A dermoscopic close-up of a skin lesion.
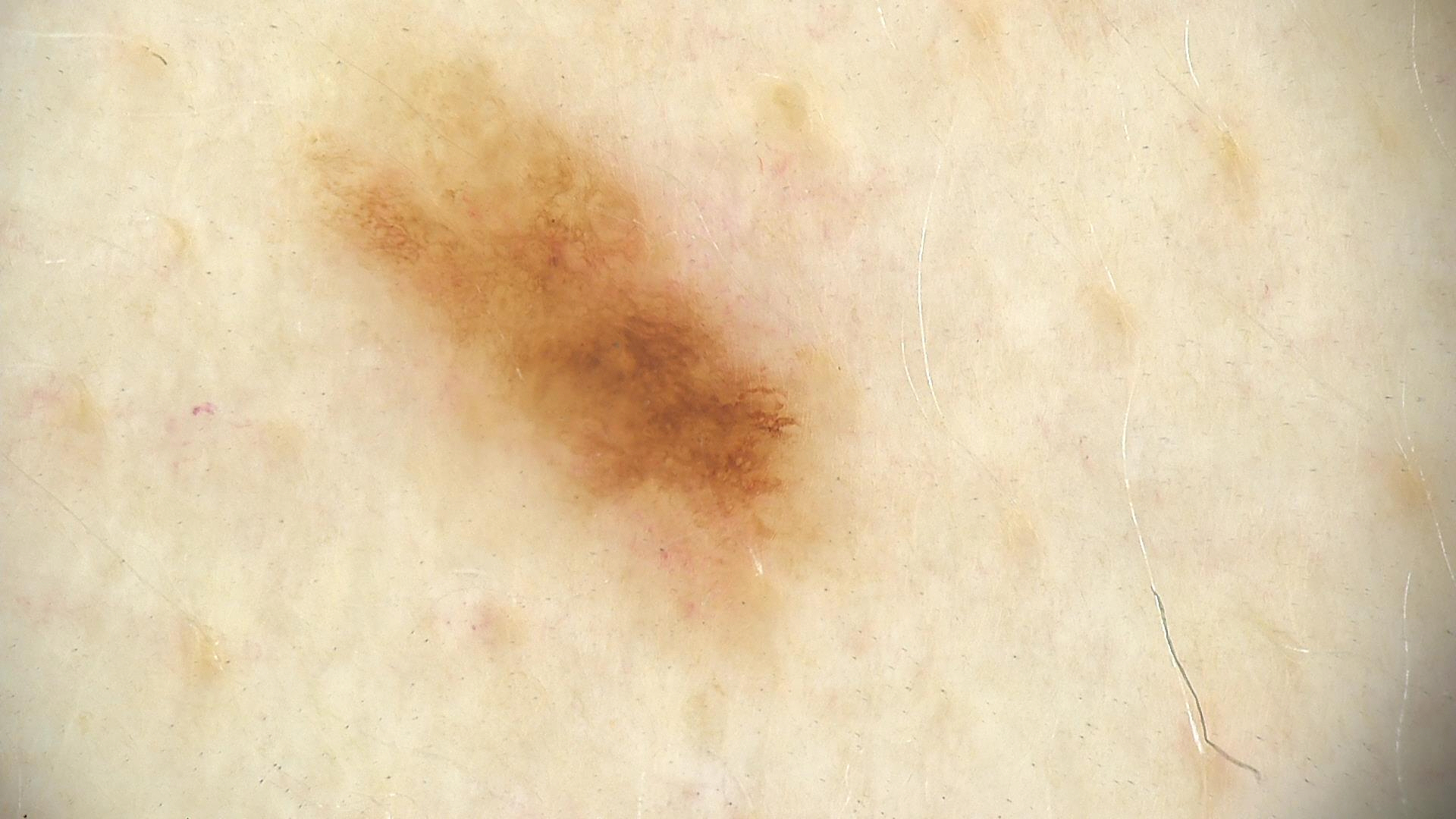diagnostic label = dysplastic junctional nevus (expert consensus).